A dermoscopic image of a skin lesion.
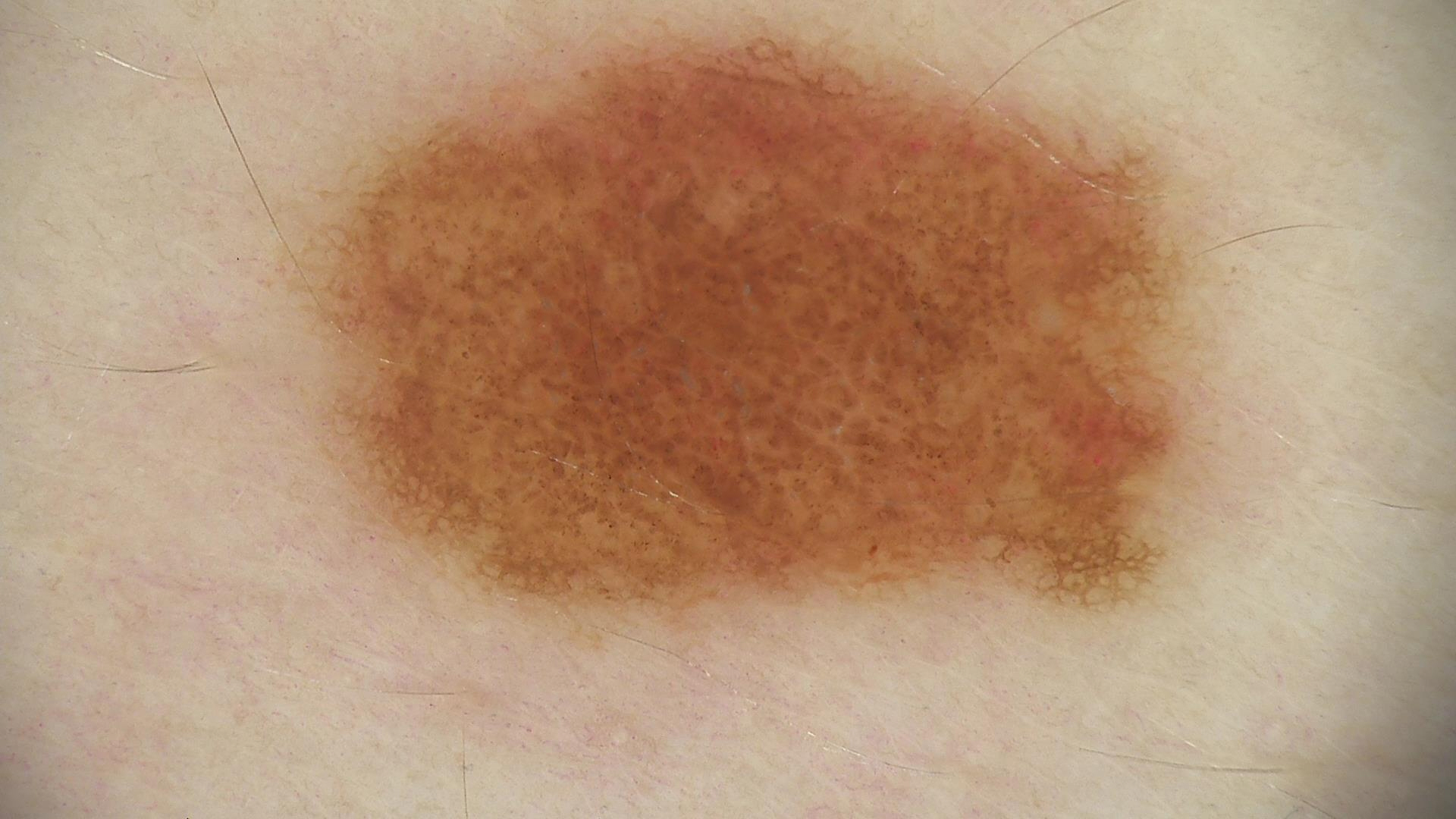The diagnosis was a dysplastic junctional nevus.